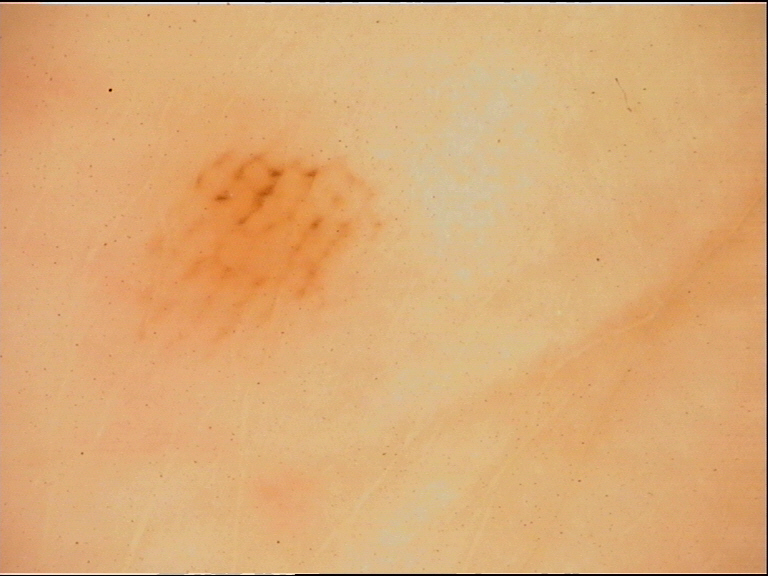A dermoscopic photograph of a skin lesion. Diagnosed as a banal lesion — an acral junctional nevus.